A skin lesion imaged with a dermatoscope.
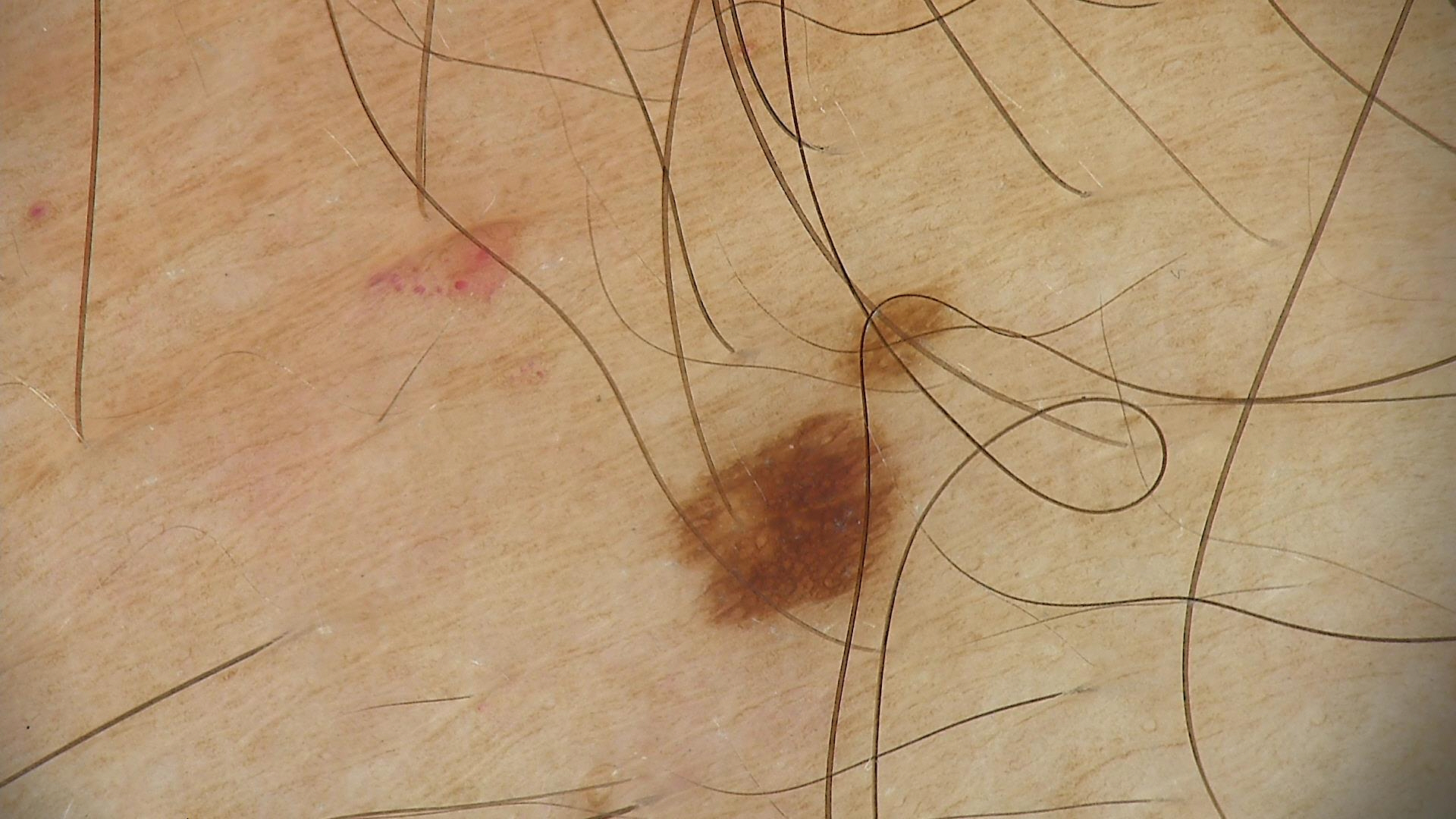{
  "diagnosis": {
    "name": "dysplastic junctional nevus",
    "code": "jd",
    "malignancy": "benign",
    "super_class": "melanocytic",
    "confirmation": "expert consensus"
  }
}